A dermoscopic view of a skin lesion.
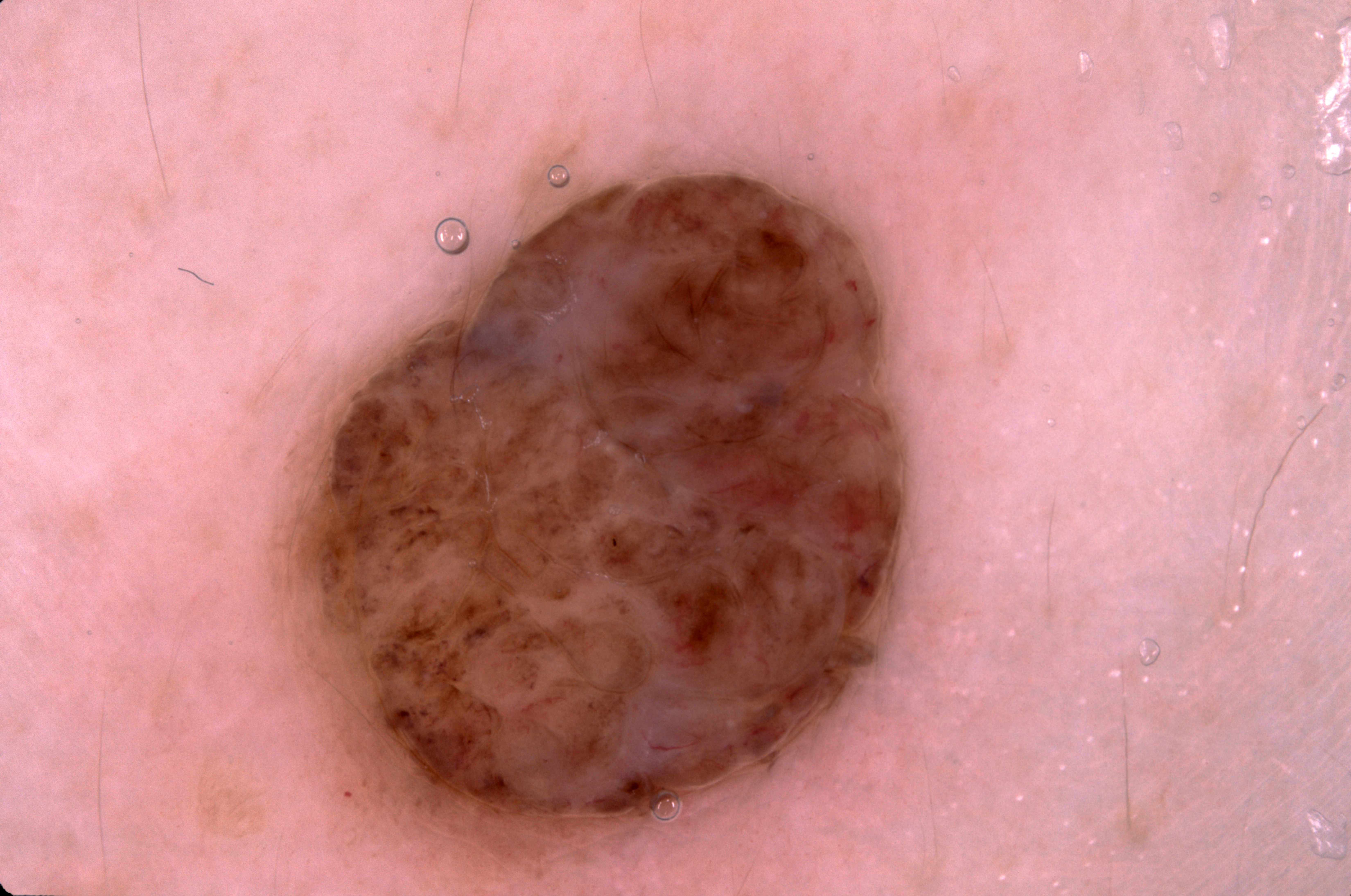lesion_location:
  bbox_xyxy:
    - 294
    - 169
    - 910
    - 862
dermoscopic_features:
  present: []
  absent:
    - streaks
    - negative network
    - pigment network
    - milia-like cysts
lesion_extent: moderate
diagnosis:
  name: melanocytic nevus
  malignancy: benign
  lineage: melanocytic
  provenance: clinical